The contributor notes itching, bothersome appearance and pain · the photograph is a close-up of the affected area · the contributor notes the condition has been present for about one day · the affected area is the arm · the lesion is described as raised or bumpy · the patient considered this a rash — 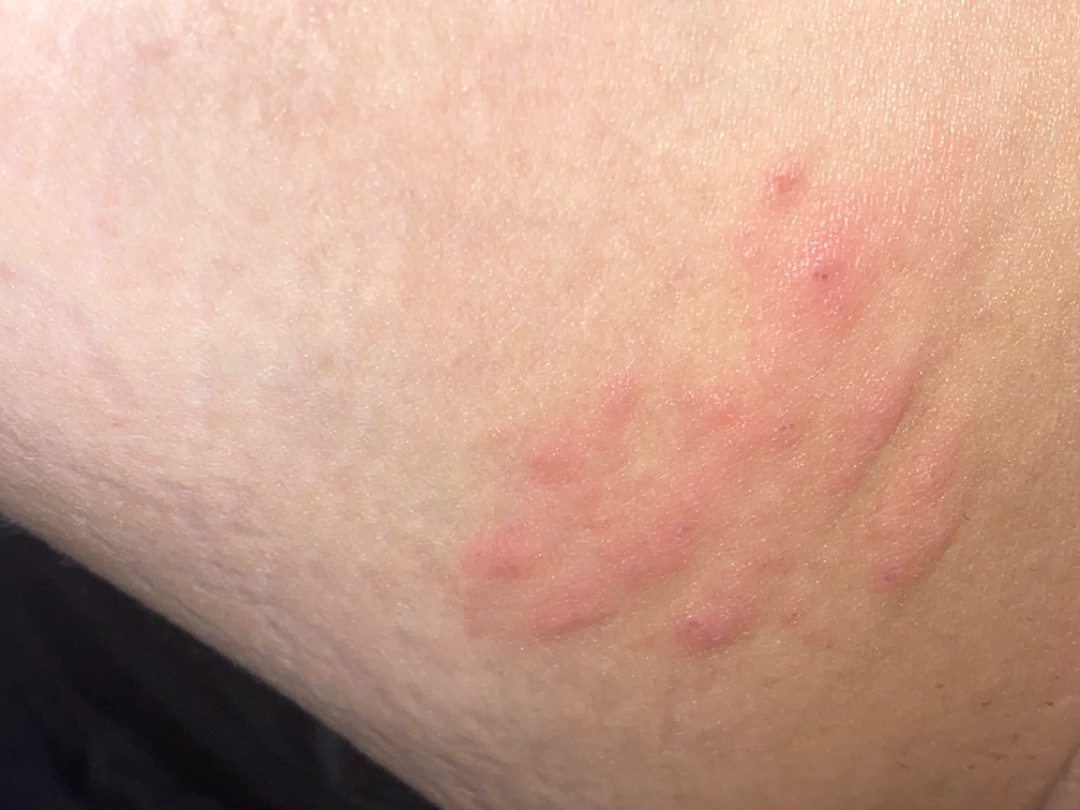| feature | finding |
|---|---|
| assessment | unable to determine |